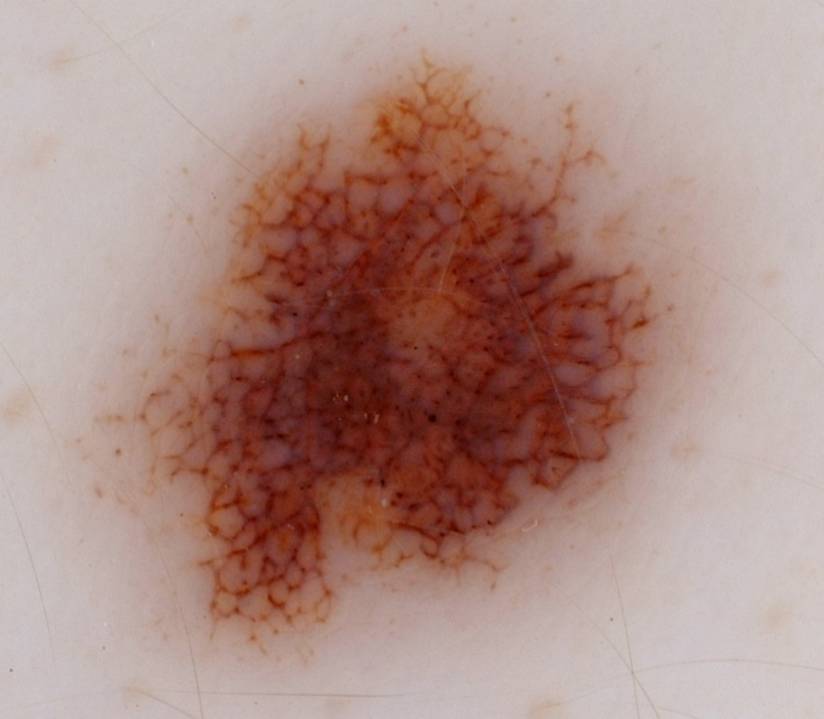image:
  modality: dermoscopy
dermoscopic_features:
  present:
    - pigment network
    - globules
  absent:
    - negative network
    - streaks
    - milia-like cysts
lesion_extent: large
lesion_location:
  bbox_xyxy:
    - 92
    - 50
    - 699
    - 662
diagnosis:
  name: melanocytic nevus
  malignancy: benign
  lineage: melanocytic
  provenance: clinical